The photograph was taken at an angle. Located on the arm, back of the hand, back of the torso, head or neck and leg. The patient is a female aged 30–39.
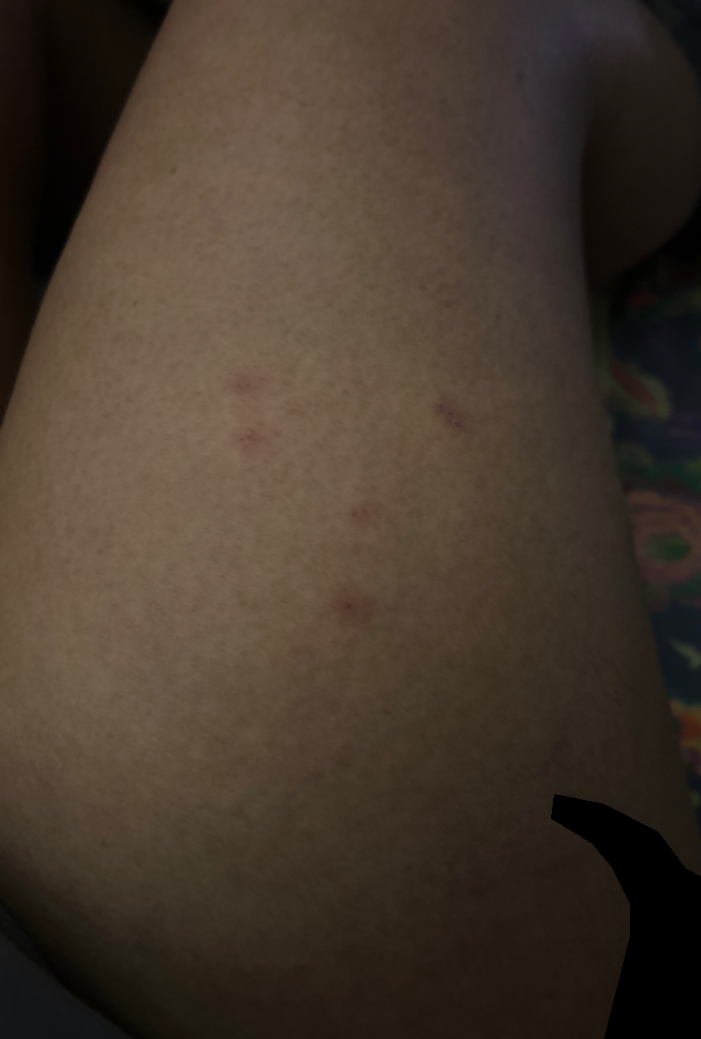Background: The patient indicates associated fatigue. The patient described the issue as skin that appeared healthy to them. The lesion is described as raised or bumpy and flat. Findings: On teledermatology review, the differential, in no particular order, includes Irritant Contact Dermatitis and Allergic Contact Dermatitis; possibly Eczema.